A female subject 60 years of age. A clinical photograph showing a skin lesion. Collected as part of a research study, without a referral diagnosis — 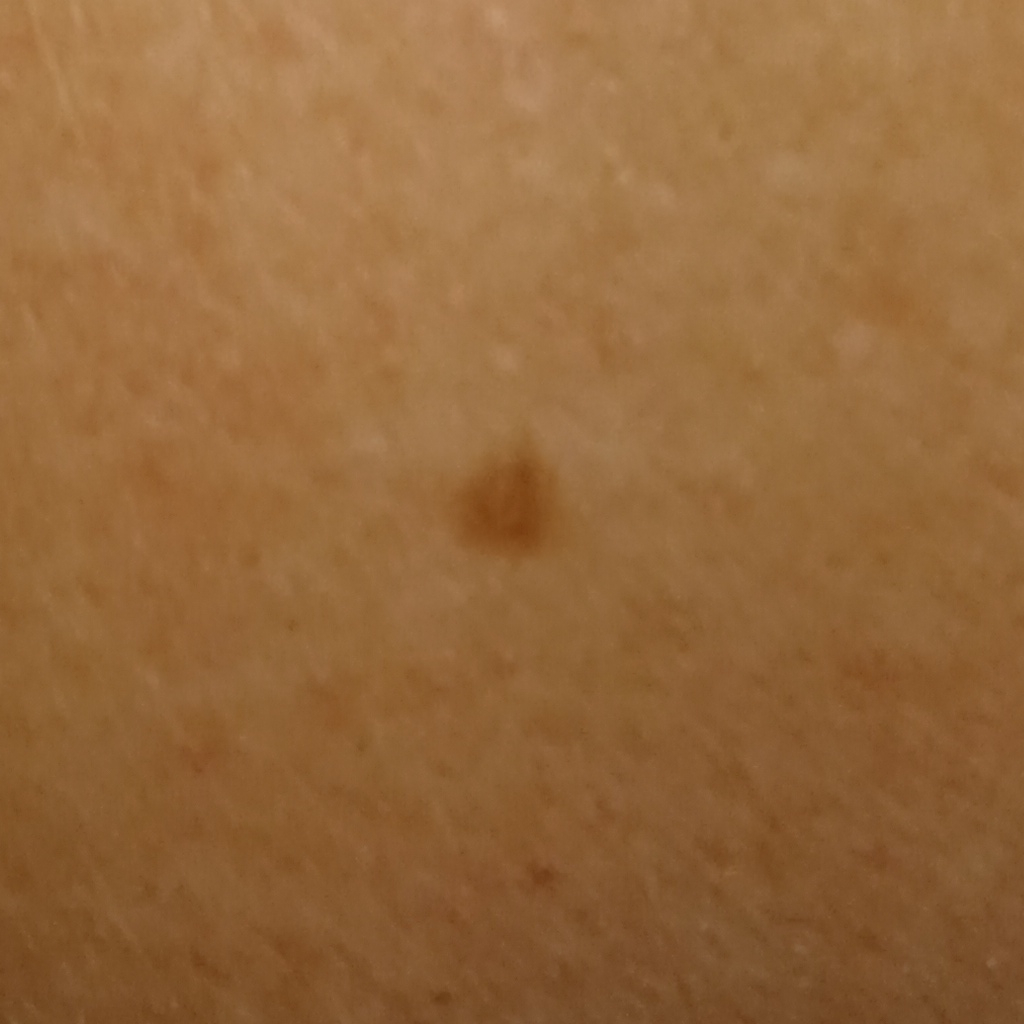body site = an arm, size = 2.8 mm, diagnostic label = melanocytic nevus (dermatologist consensus).